A dermoscopy image of a single skin lesion:
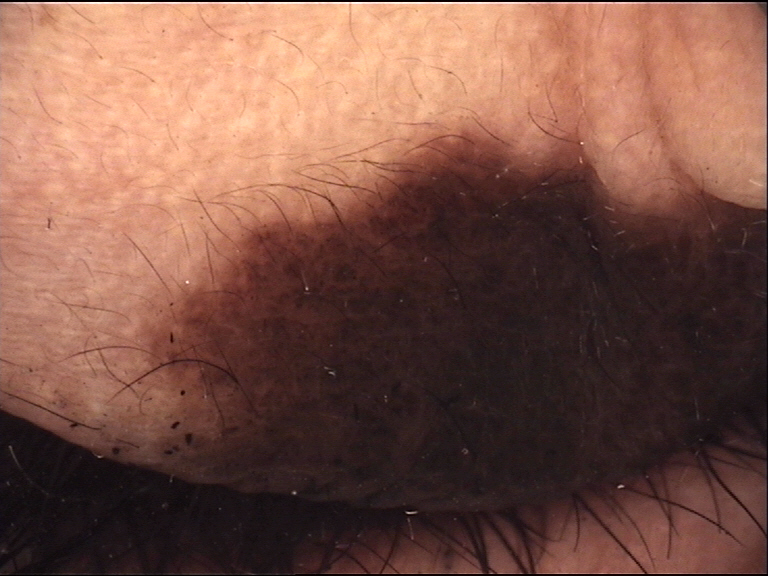The morphology is that of a banal lesion. The diagnostic label was a congenital compound nevus.